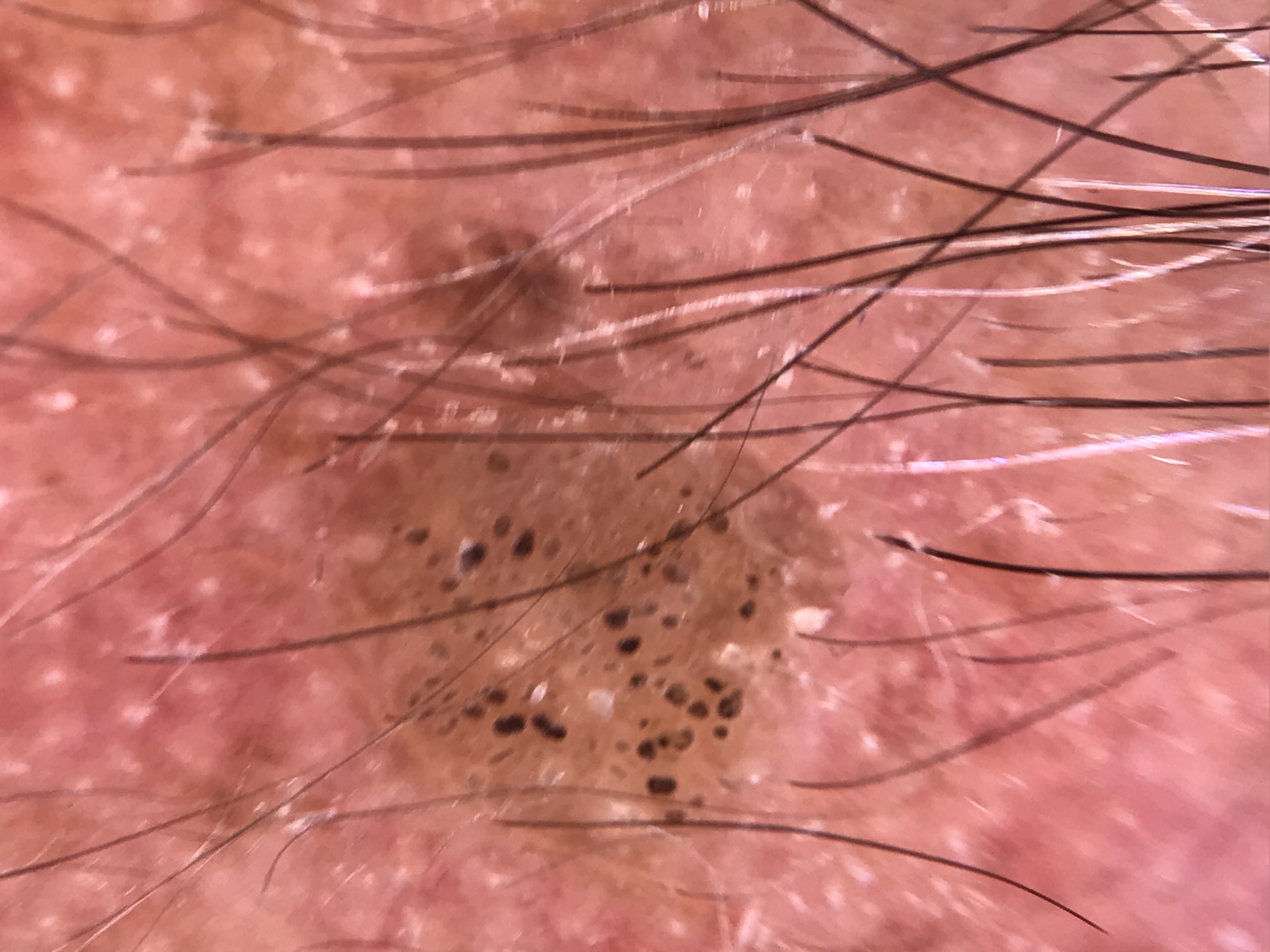A dermoscopy image of a single skin lesion. The morphology is that of a keratinocytic lesion. The diagnostic label was a benign lesion — a seborrheic keratosis.